A dermoscopic close-up of a skin lesion.
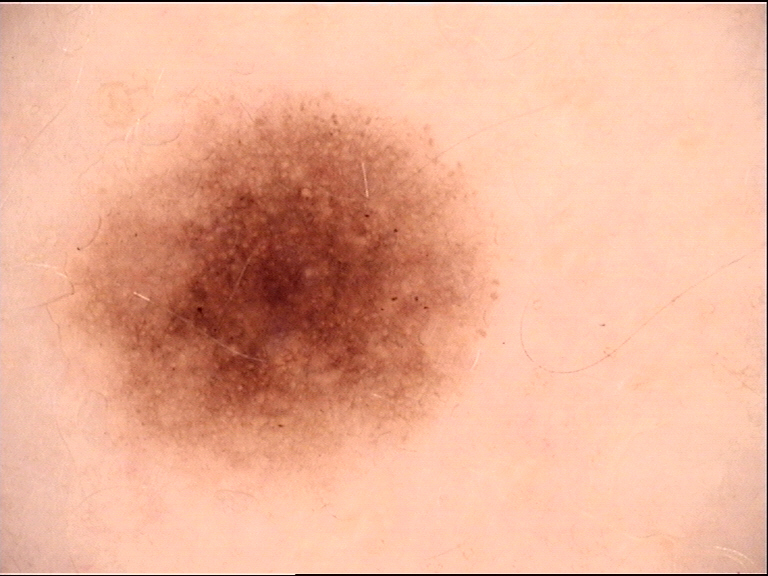Case:
- assessment — dysplastic junctional nevus (expert consensus)